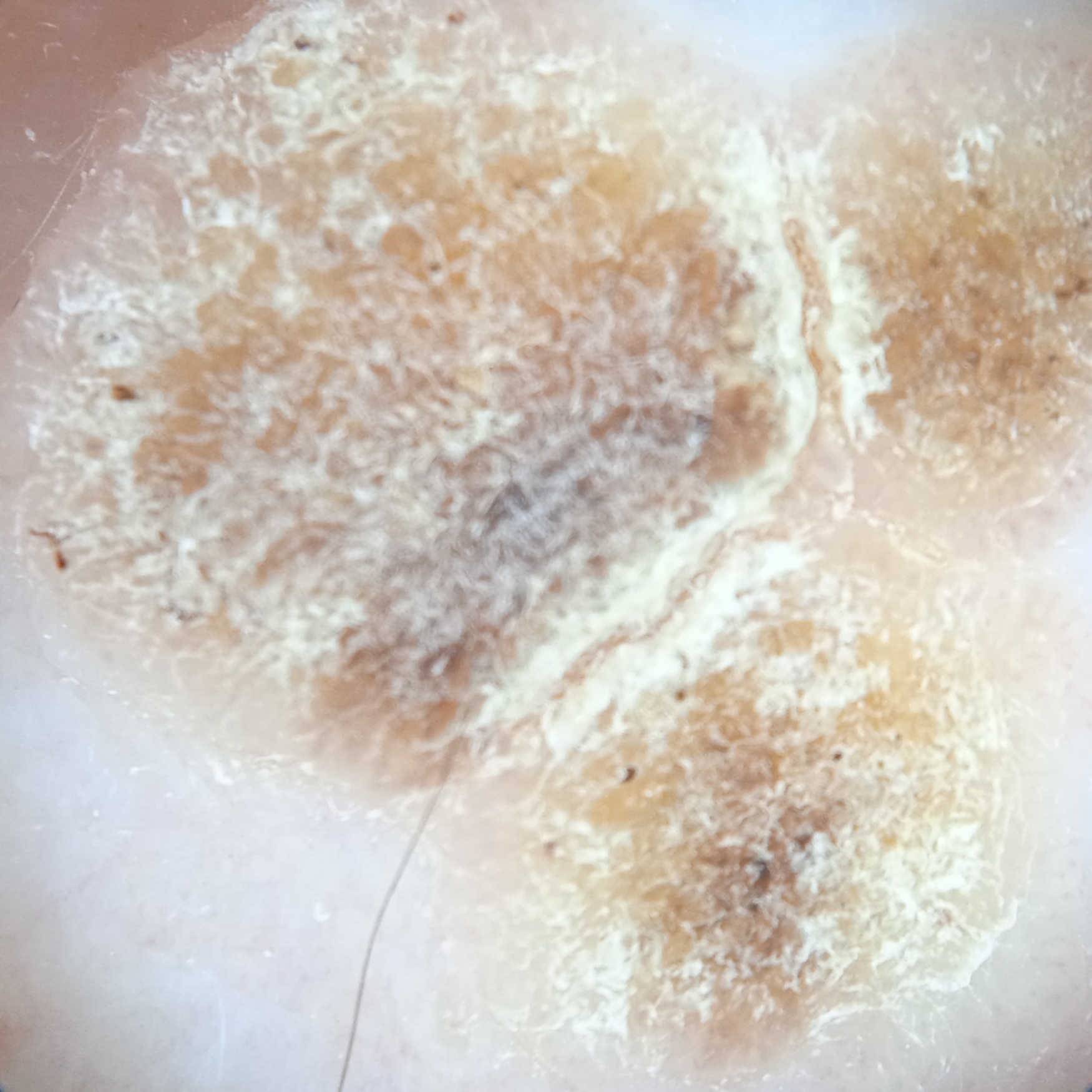  referral: research study (no referral diagnosis)
  patient:
    age: 77
    sex: male
  image: dermoscopic image
  lesion_location: the back
  lesion_size:
    diameter_mm: 14.2
  diagnosis:
    name: seborrheic keratosis
    malignancy: benign